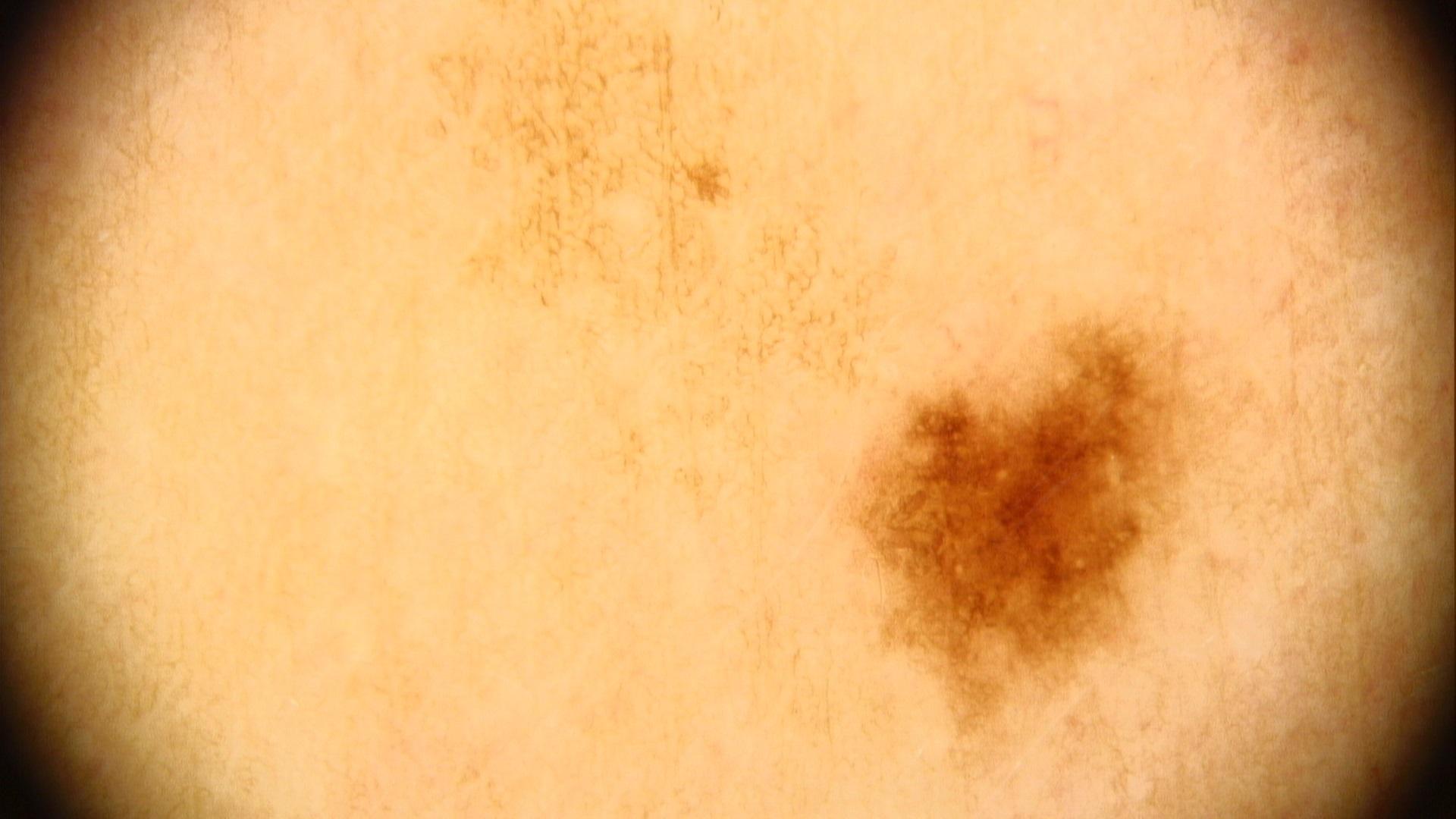assessment — Nevus.